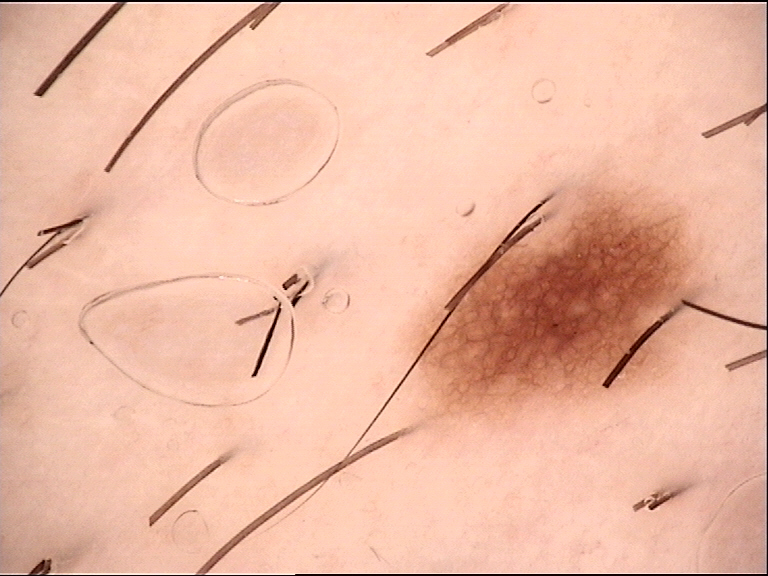Impression:
Diagnosed as a dysplastic junctional nevus.